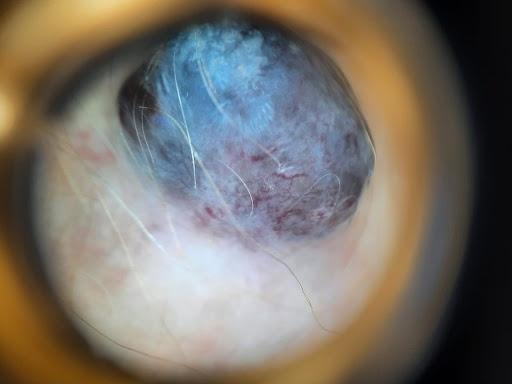Findings:
• skin type · I
• subject · male, aged 83 or over
• image · contact-polarized dermoscopy
• site · an upper extremity
• diagnosis · Melanoma (biopsy-proven)